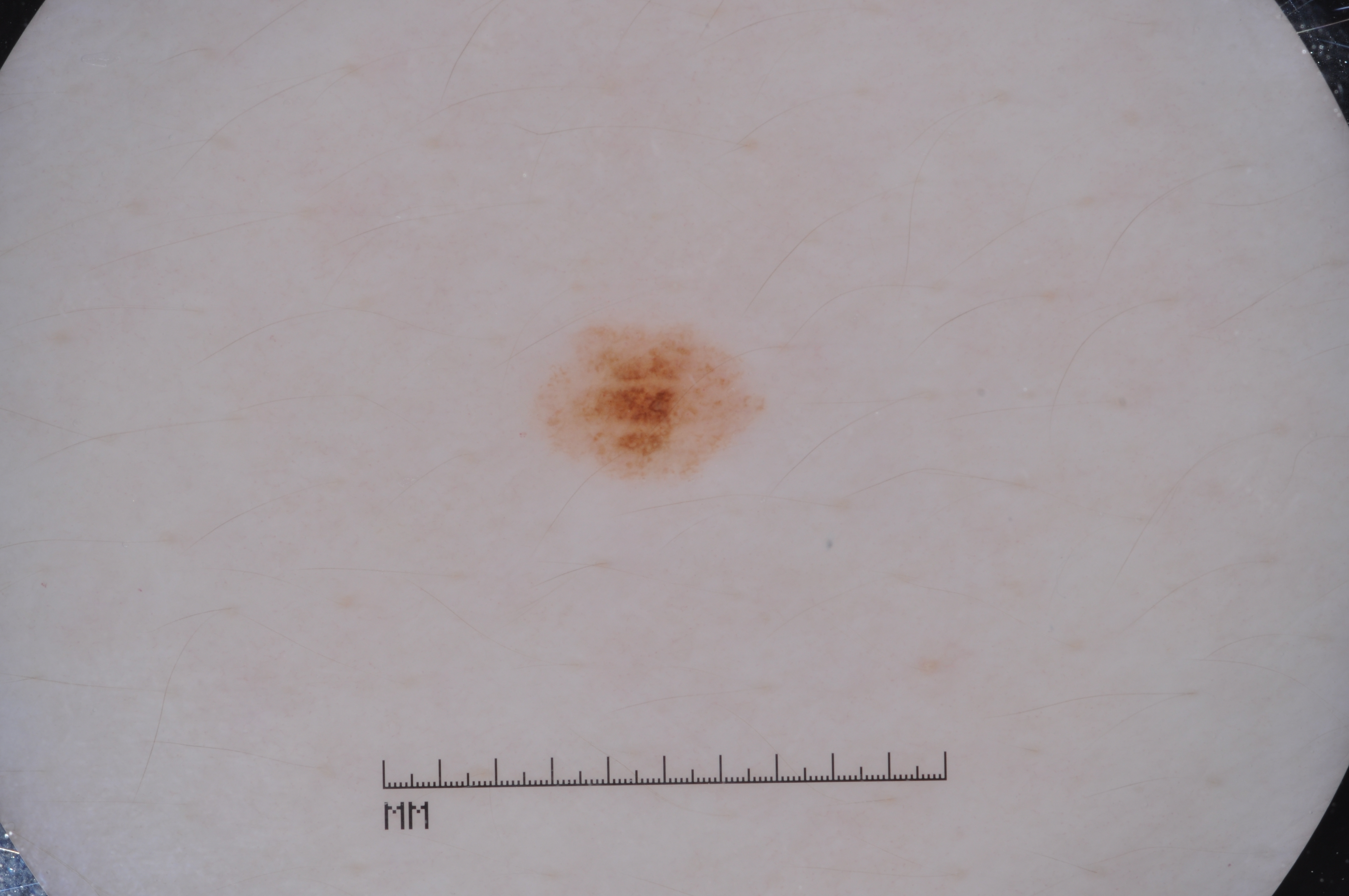This is a dermoscopic photograph of a skin lesion. A female subject, about 30 years old. The lesion takes up about 2% of the image. Dermoscopic review identifies no milia-like cysts, streaks, negative network, or pigment network. In (x1, y1, x2, y2) order, the lesion's extent is <bbox>559, 337, 738, 469</bbox>. Consistent with a melanocytic nevus.